Female subject, age 18–29 · an image taken at an angle · the affected area is the arm.
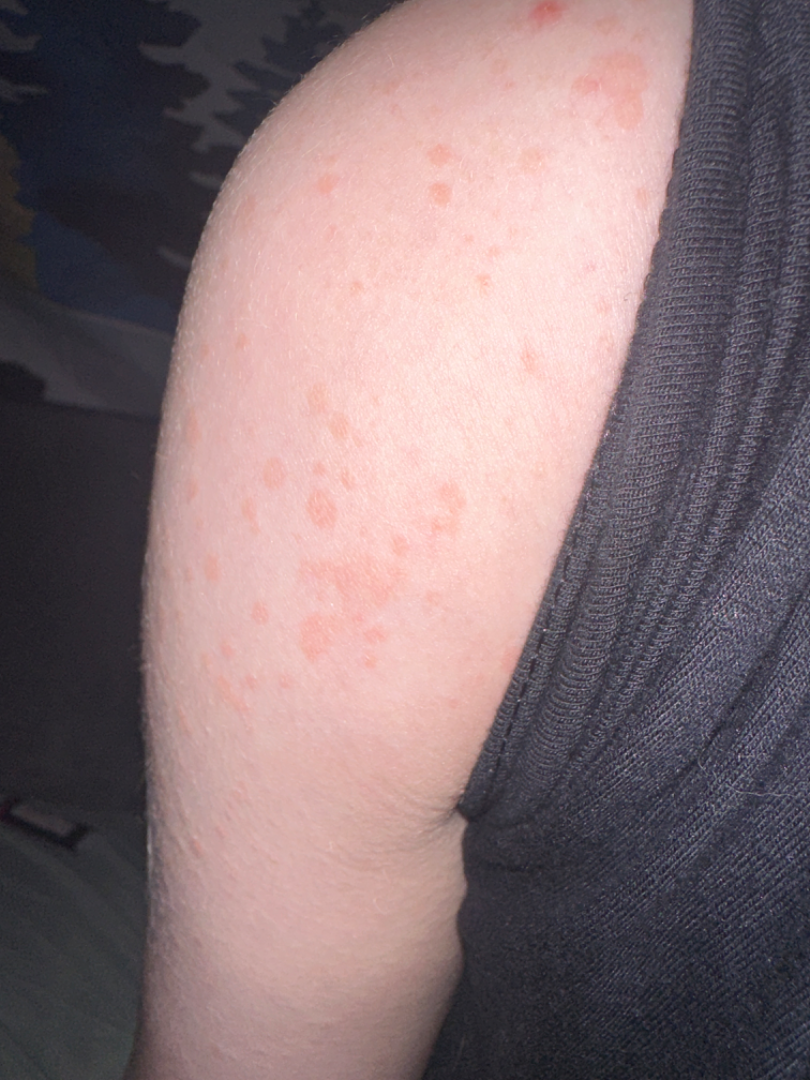Q: What was the assessment?
A: unable to determine
Q: Duration?
A: three to twelve months
Q: How does the patient describe it?
A: a rash
Q: What symptoms does the patient report?
A: enlargement